Reported lesion symptoms include bothersome appearance, burning, pain and enlargement; the lesion involves the leg; the photo was captured at a distance.
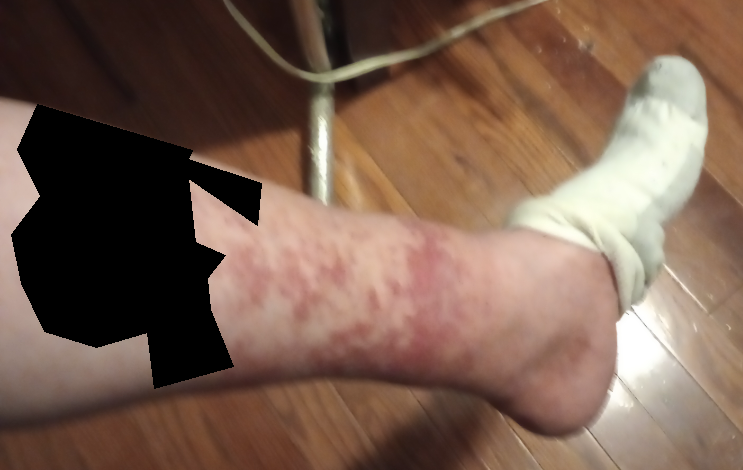Findings:
The dermatologist could not determine a likely condition from the photograph alone.